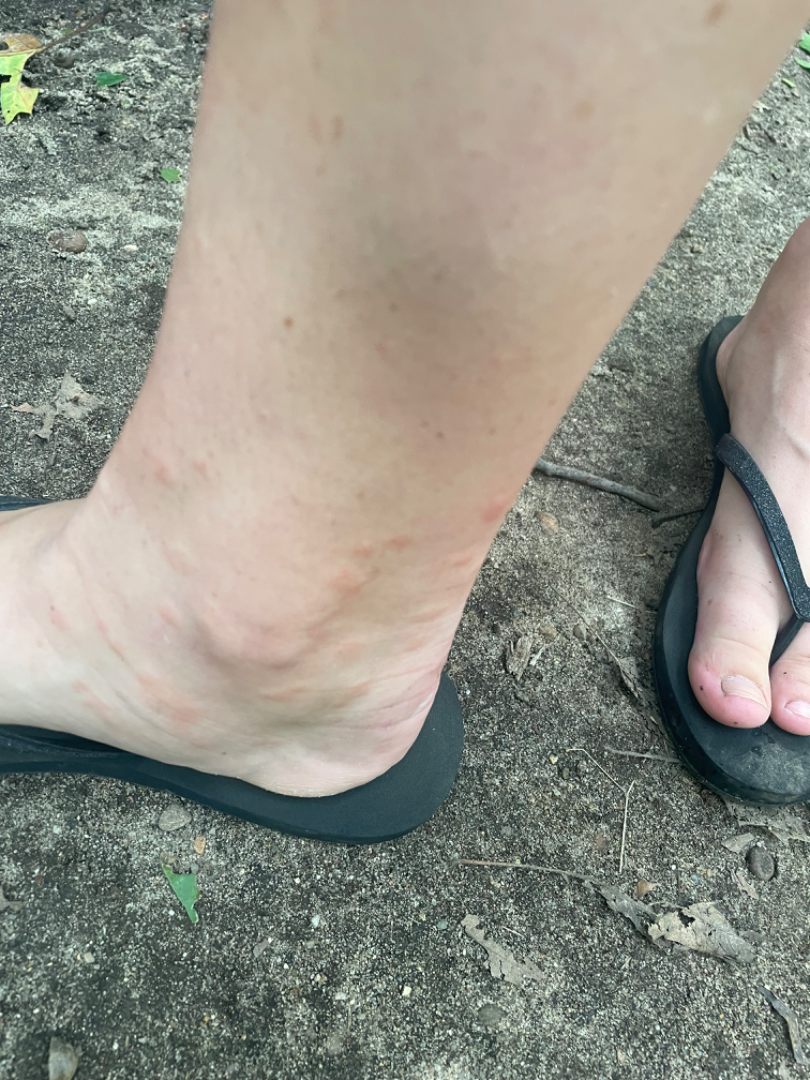The condition has been present for about one day.
Reported lesion symptoms include bothersome appearance and itching.
The lesion involves the top or side of the foot.
Close-up view.
The subject is 18–29, female.
Fitzpatrick II; non-clinician graders estimated Monk skin tone scale 1 or 2.
The patient described the issue as a rash.
The patient indicates the lesion is raised or bumpy.
On photographic review by a dermatologist, the leading impression is Urticaria.